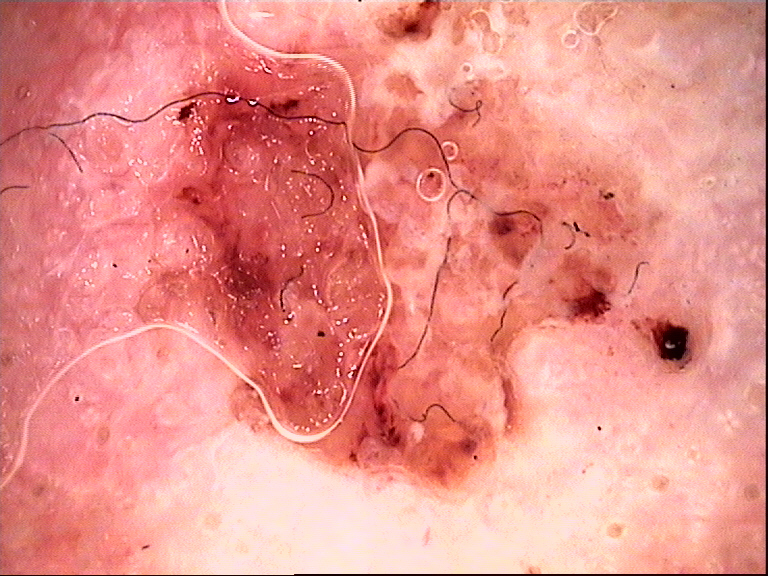category=keratinocytic; class=squamous cell carcinoma (biopsy-proven).